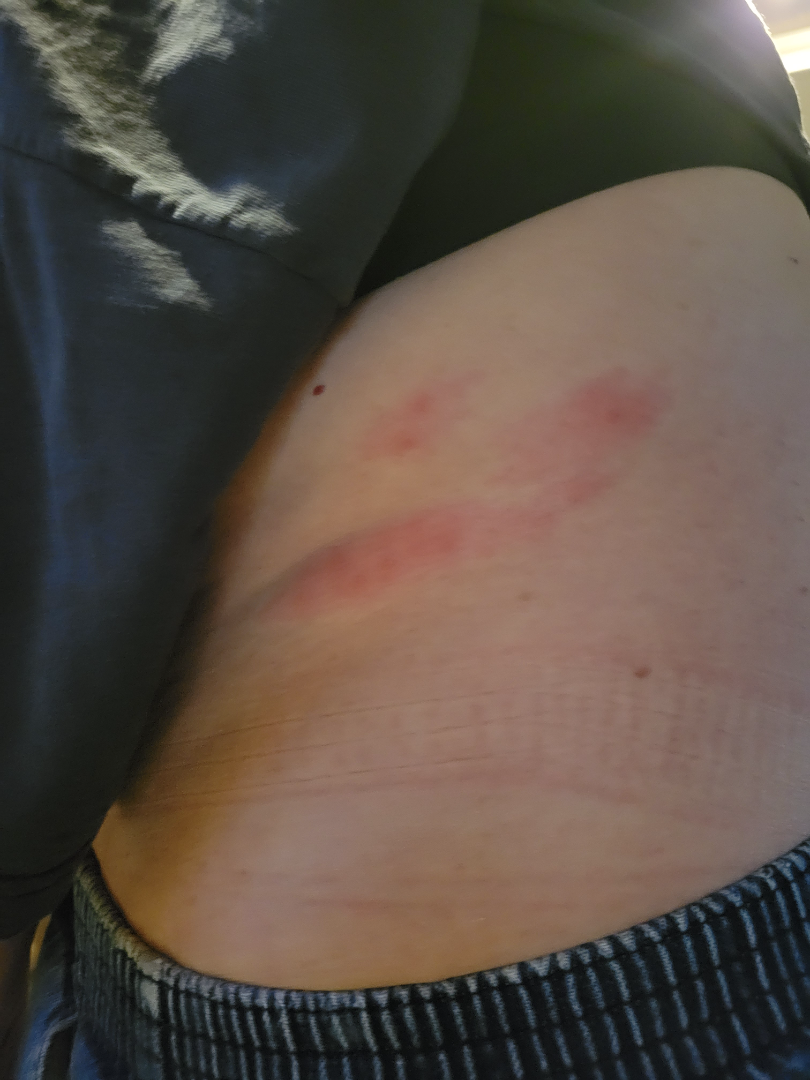  differential:
    leading:
      - Herpes Zoster